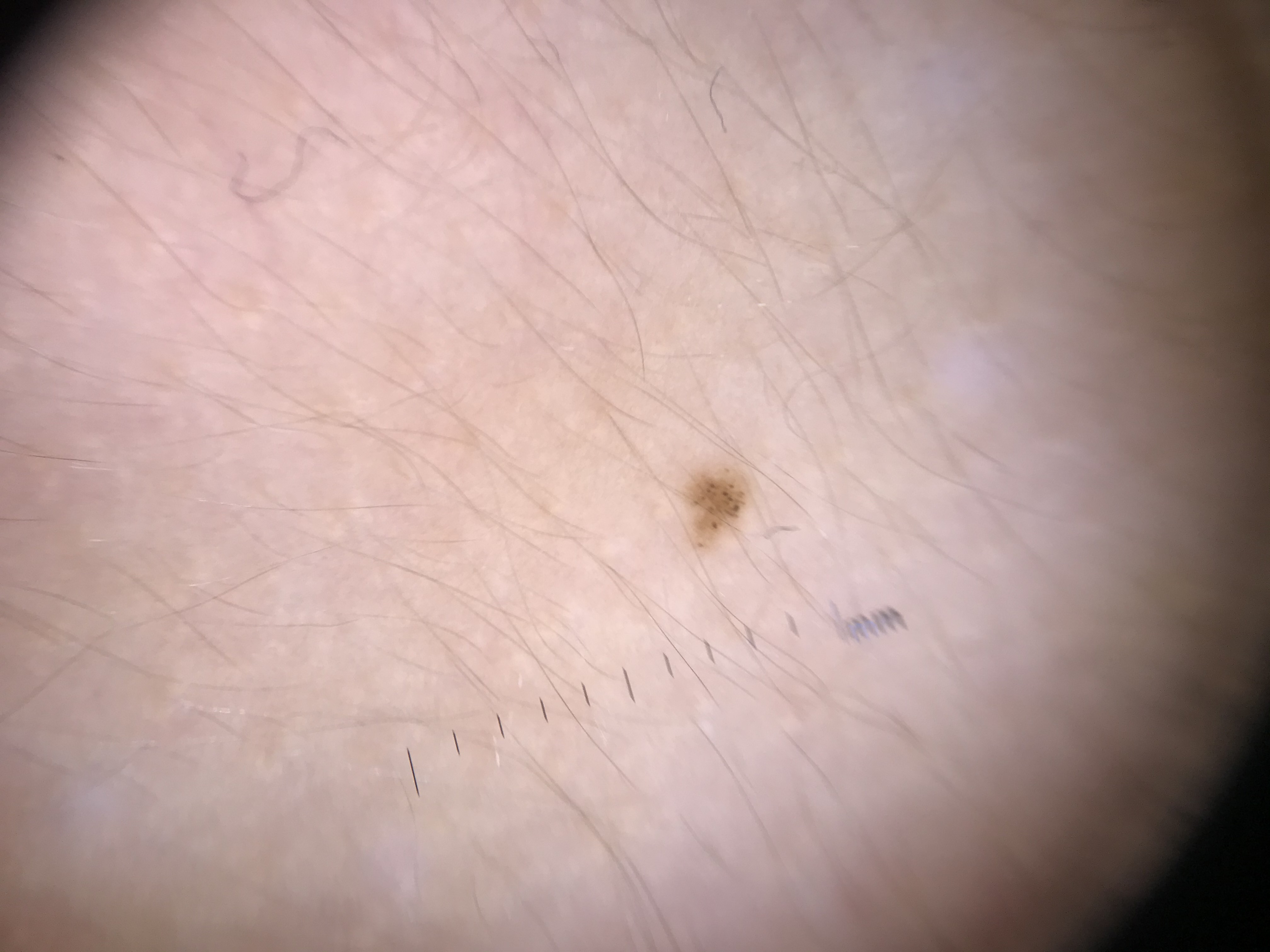A dermoscopic close-up of a skin lesion. Consistent with a banal lesion — a junctional nevus.